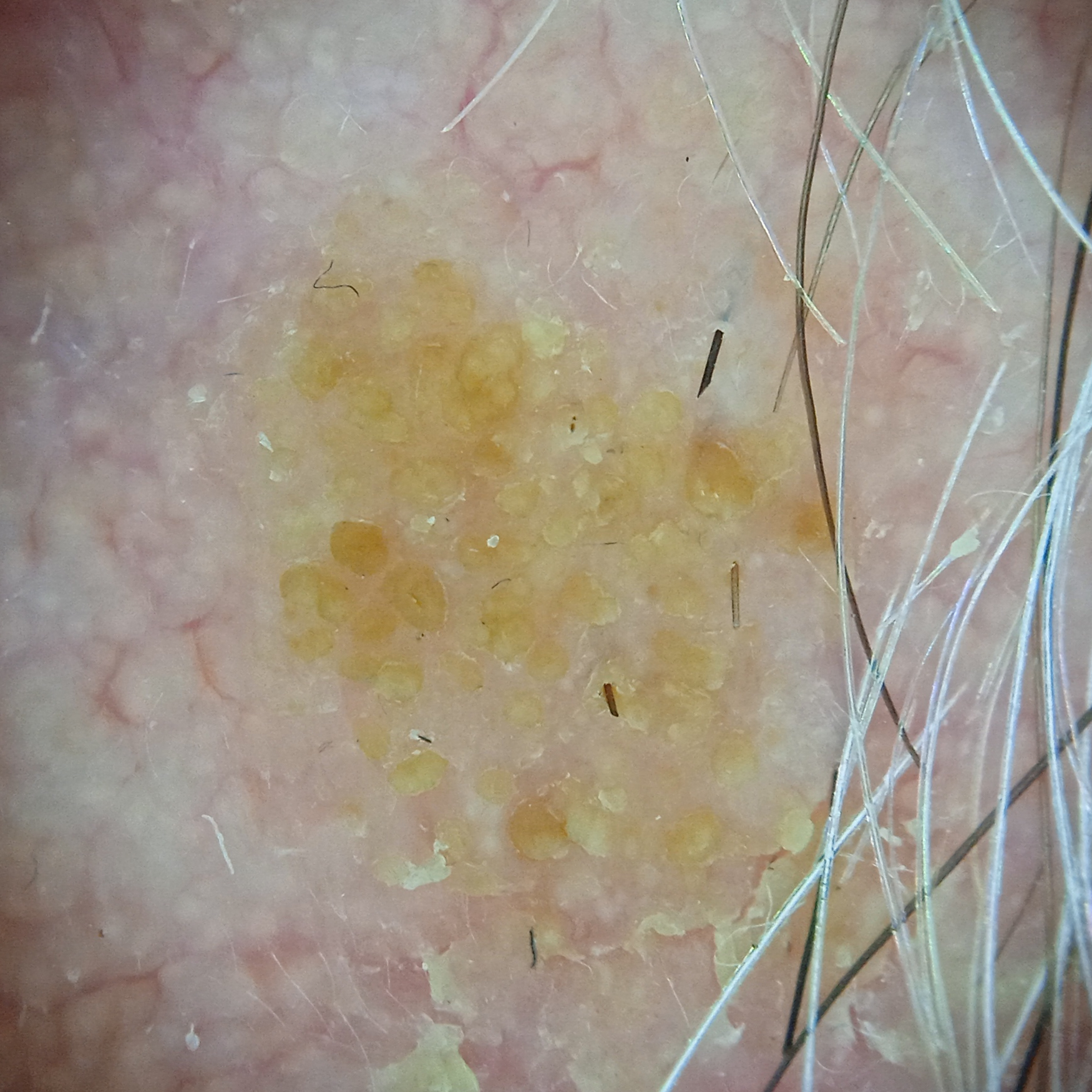clinical context=research study (no referral diagnosis) | imaging=dermatoscopic image | subject=male, 89 years old | sun reaction=skin reddens painfully with sun exposure | location=the face | size=8.8 mm | assessment=seborrheic keratosis (dermatologist consensus).